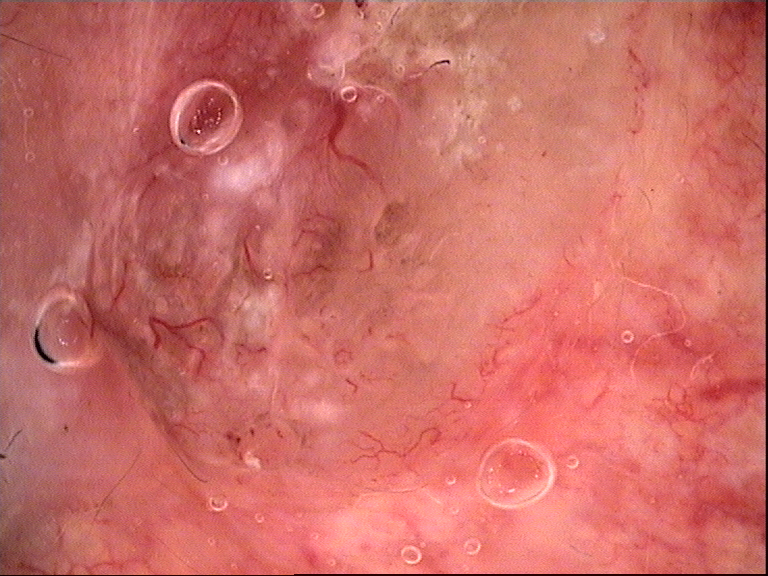label — basal cell carcinoma (biopsy-proven)